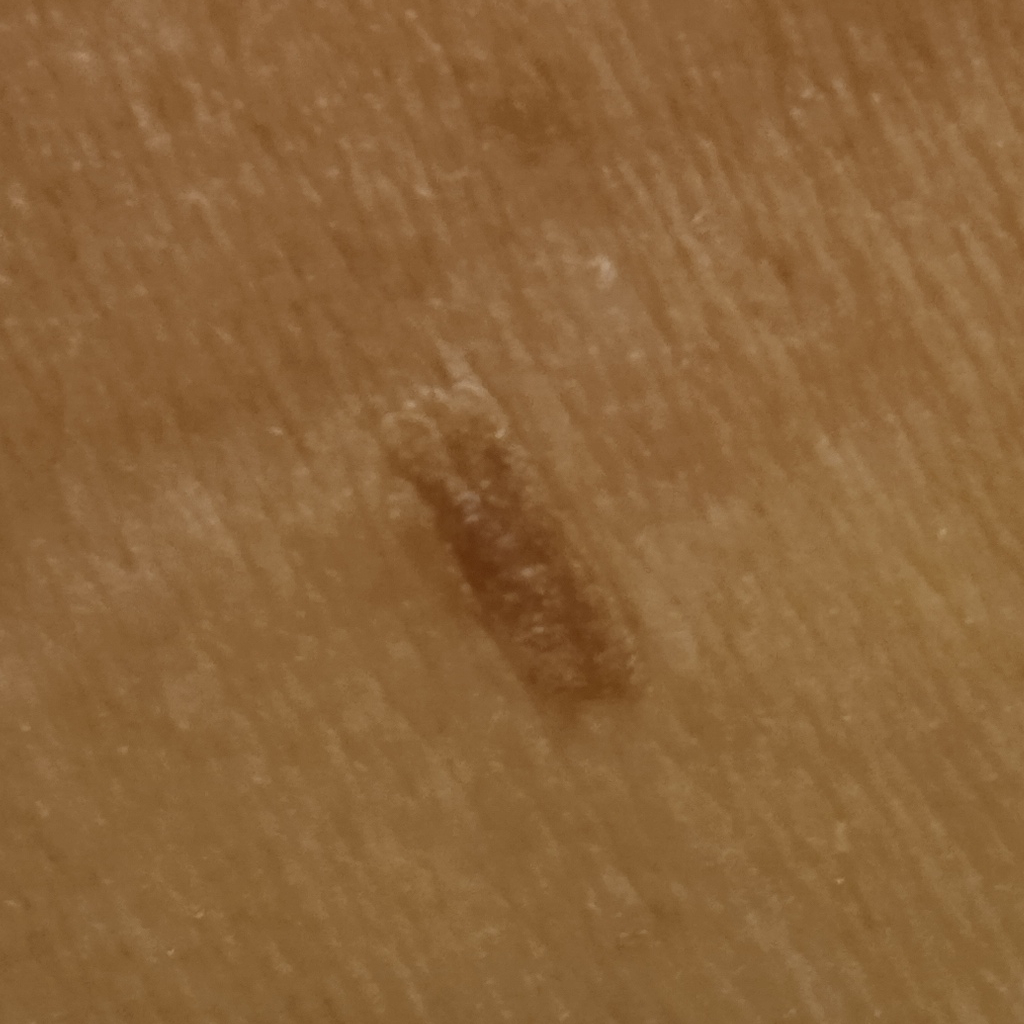Clinical context: Collected as part of a research study, without a referral diagnosis. A clinical photograph showing a skin lesion. Impression: Dermatologist review favored a seborrheic keratosis.